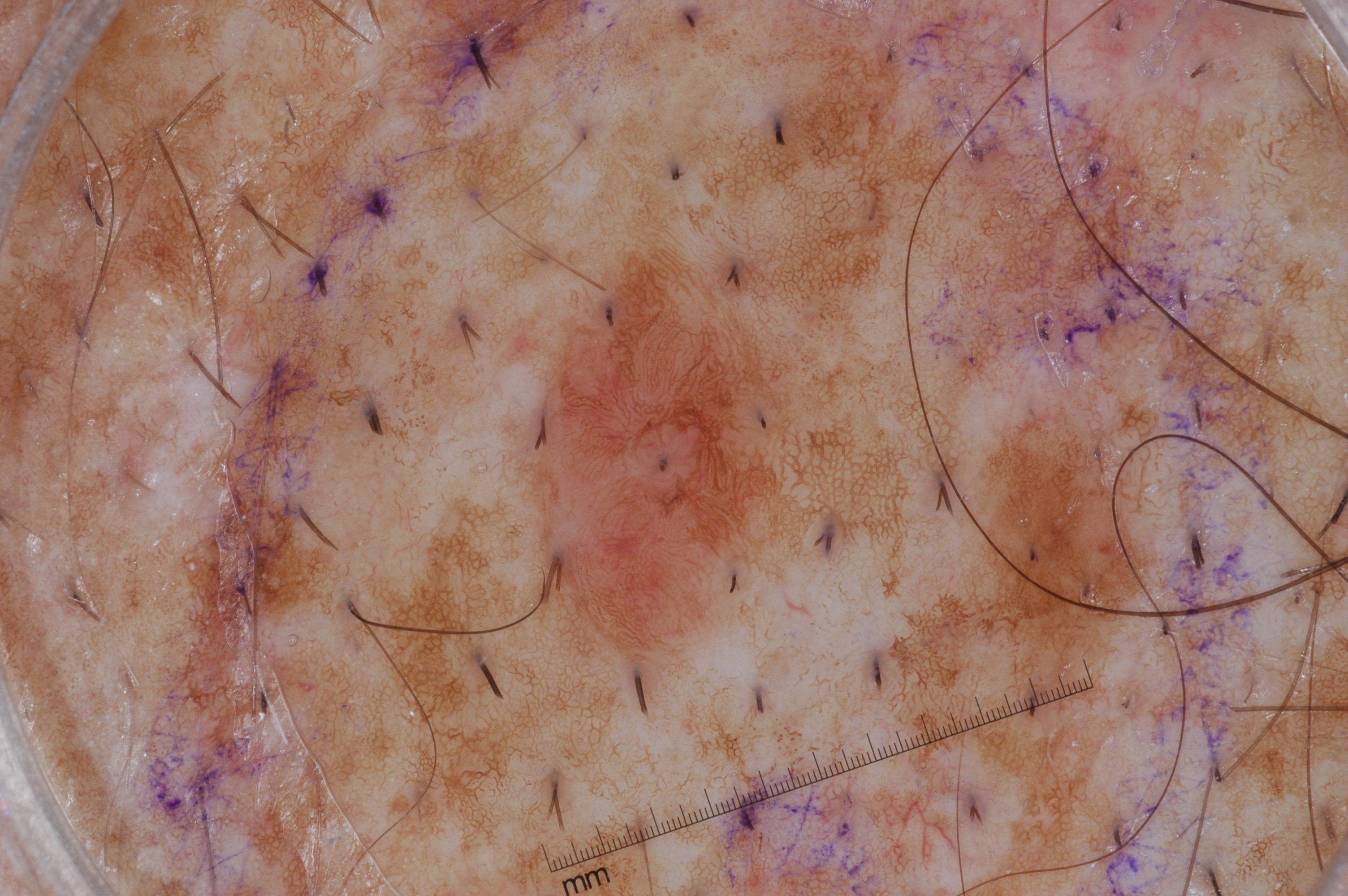Notes:
- image type — dermoscopic image
- patient — male, roughly 55 years of age
- dermoscopic features — pigment network; absent: streaks, milia-like cysts, and negative network
- lesion location — x1=523 y1=245 x2=793 y2=665
- lesion size — ~7% of the field
- diagnostic label — a melanocytic nevus, a benign lesion